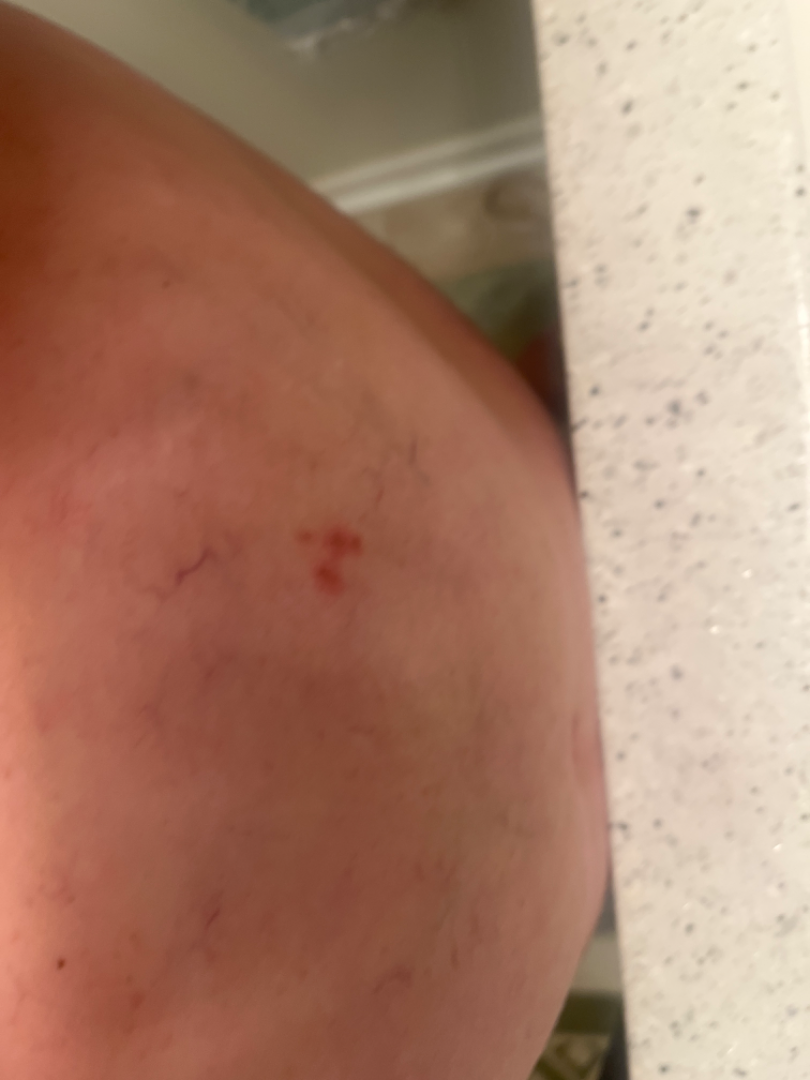The photograph was taken at a distance.
The reviewing dermatologist's impression was: most consistent with Insect Bite.